A dermoscopic image of a skin lesion: 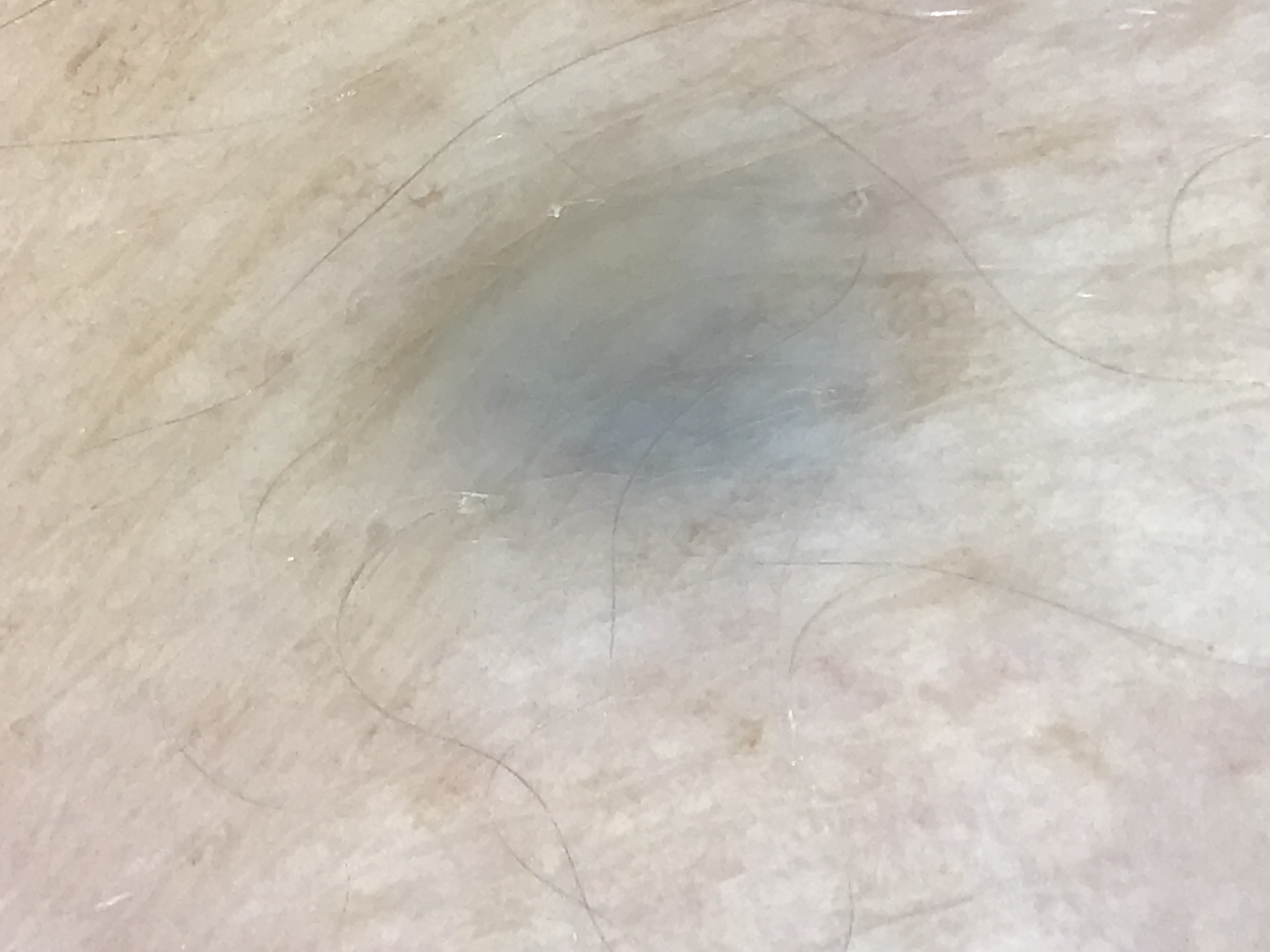class = blue nevus (expert consensus).